A male patient, approximately 45 years of age; a dermoscopic view of a skin lesion:
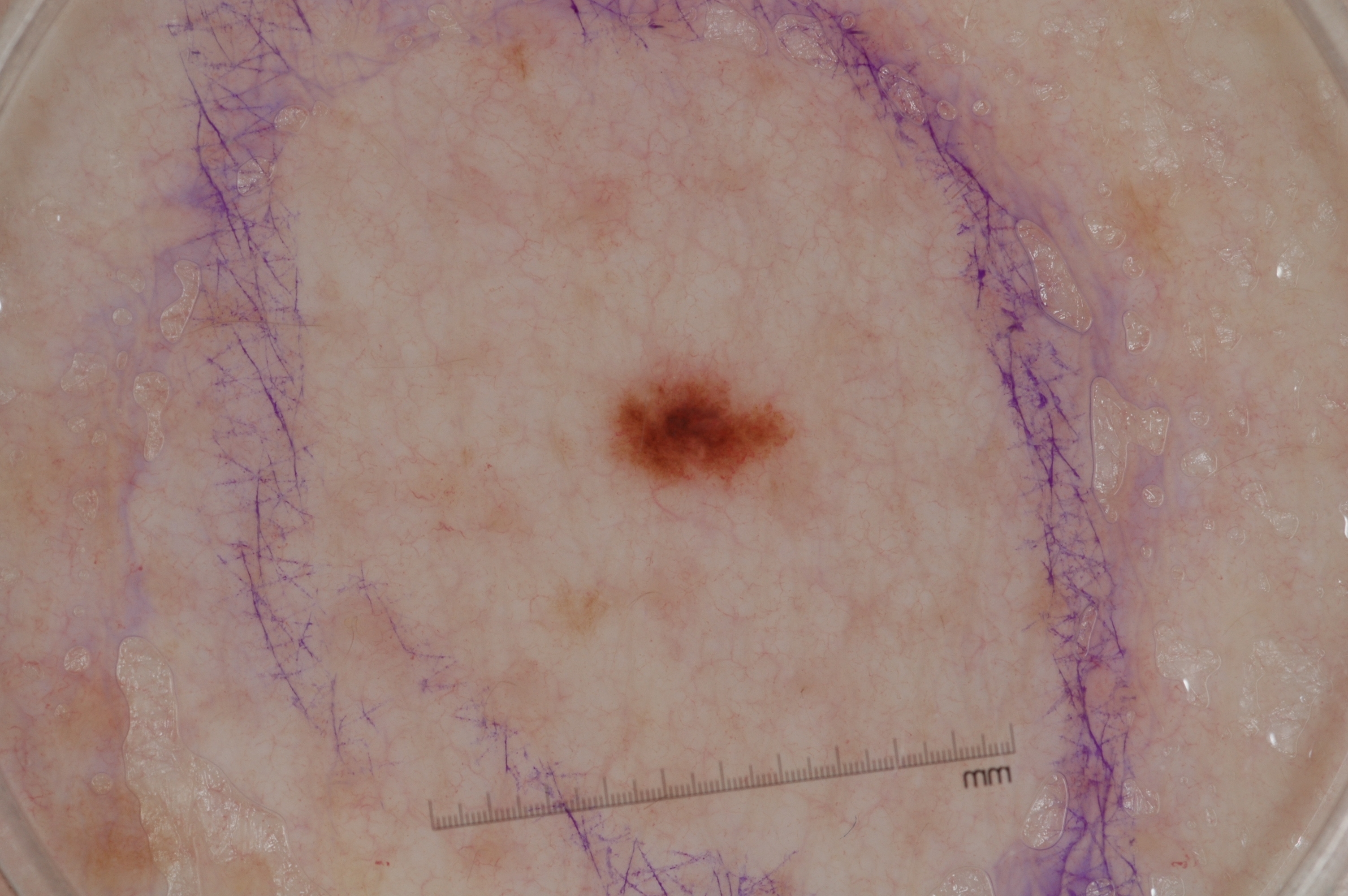On dermoscopy, the lesion shows no milia-like cysts, negative network, pigment network, or streaks. With coordinates (x1, y1, x2, y2), the lesion spans <bbox>611, 364, 790, 490</bbox>. The clinical diagnosis was a melanocytic nevus.